A dermatoscopic image of a skin lesion:
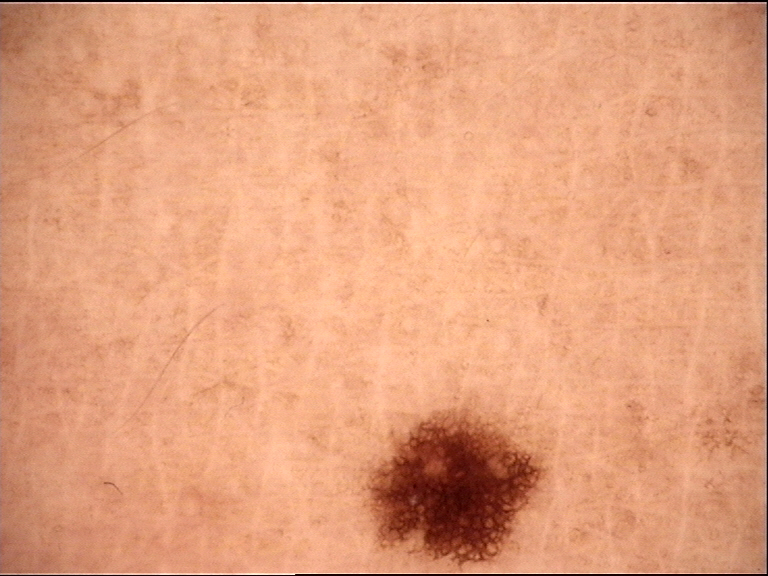  diagnosis:
    name: dysplastic junctional nevus
    code: jd
    malignancy: benign
    super_class: melanocytic
    confirmation: expert consensus